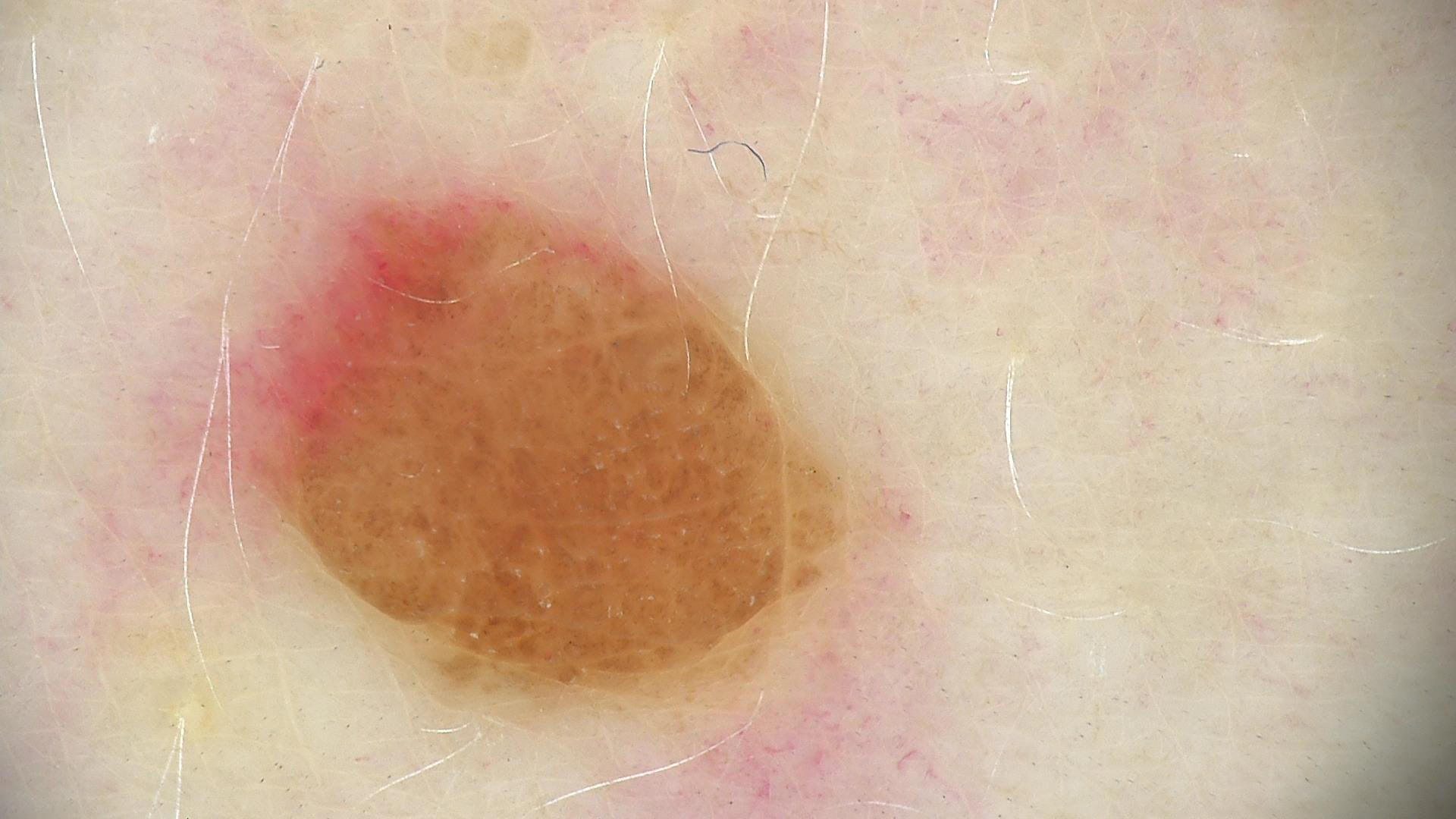<lesion>
<image>dermoscopy</image>
<diagnosis>
<name>dermal nevus</name>
<code>db</code>
<malignancy>benign</malignancy>
<super_class>melanocytic</super_class>
<confirmation>expert consensus</confirmation>
</diagnosis>
</lesion>